A female subject aged 78 · the patient says their skin tans without first burning · collected as part of a research study, without a referral diagnosis · numerous moles by the patient's own estimate.
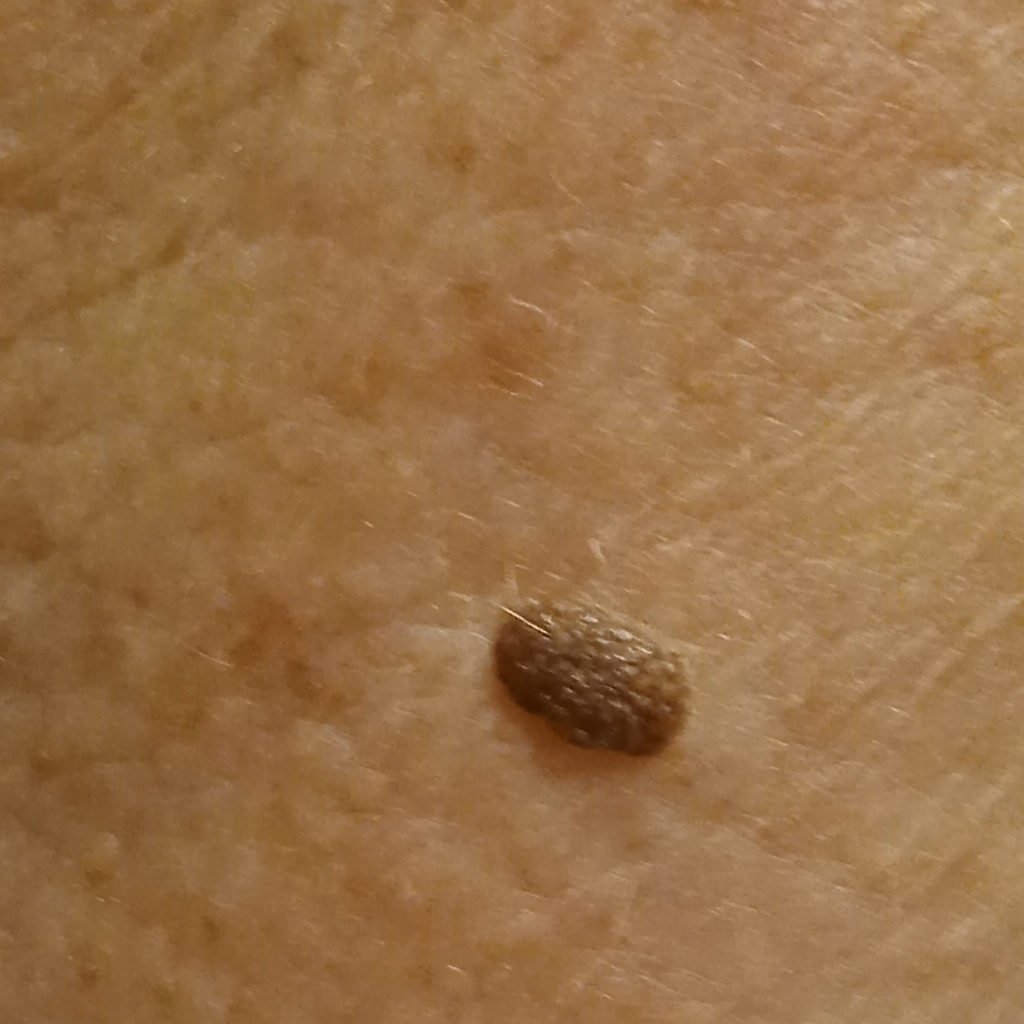Findings:
The lesion involves an arm. The lesion is about 5.6 mm across.
Conclusion:
The diagnostic impression was a seborrheic keratosis.